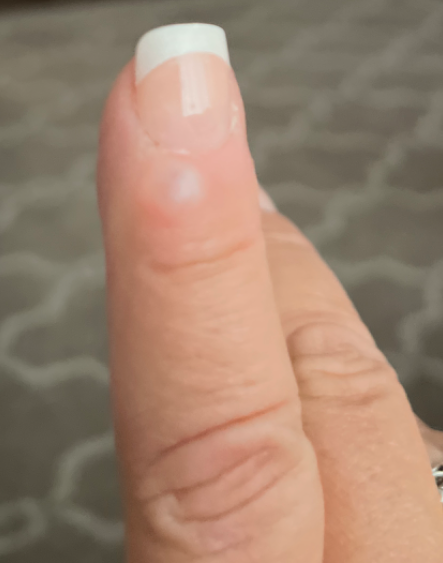Findings: The case was difficult to assess from the available photograph. Background: An image taken at a distance. Reported lesion symptoms include enlargement and bothersome appearance. The patient indicates the lesion is raised or bumpy. The patient described the issue as a growth or mole. The back of the hand is involved. The patient indicates the condition has been present for one to three months. Skin tone: lay reviewers estimated MST 3 (US pool) or 2 (India pool).